Close-up view; the lesion involves the back of the torso.
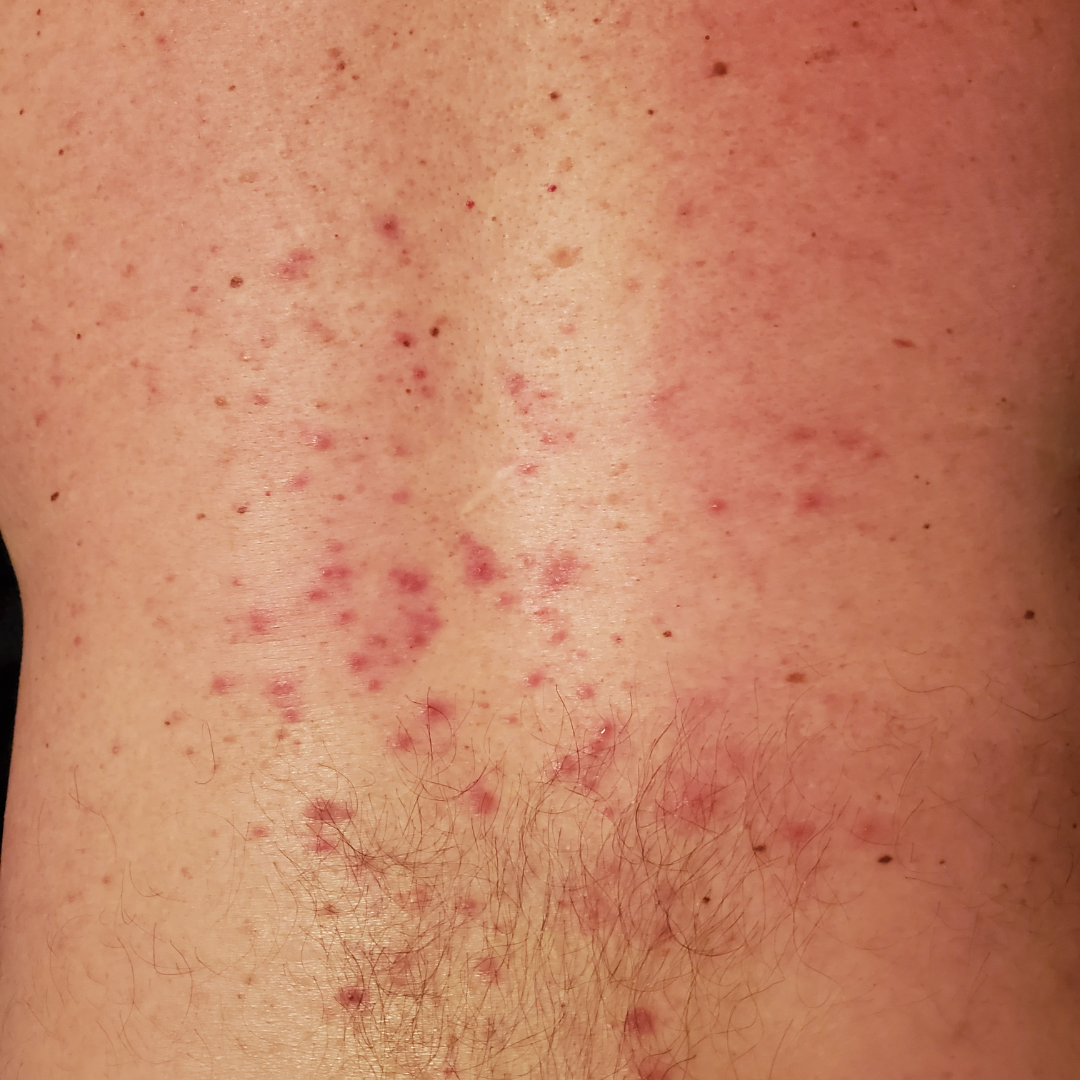The case was difficult to assess from the available photograph. The contributor notes the condition has been present for one to three months. The lesion is associated with pain, burning and itching. The contributor notes the lesion is raised or bumpy and fluid-filled. The patient considered this a rash.